A dermoscopic photograph of a skin lesion.
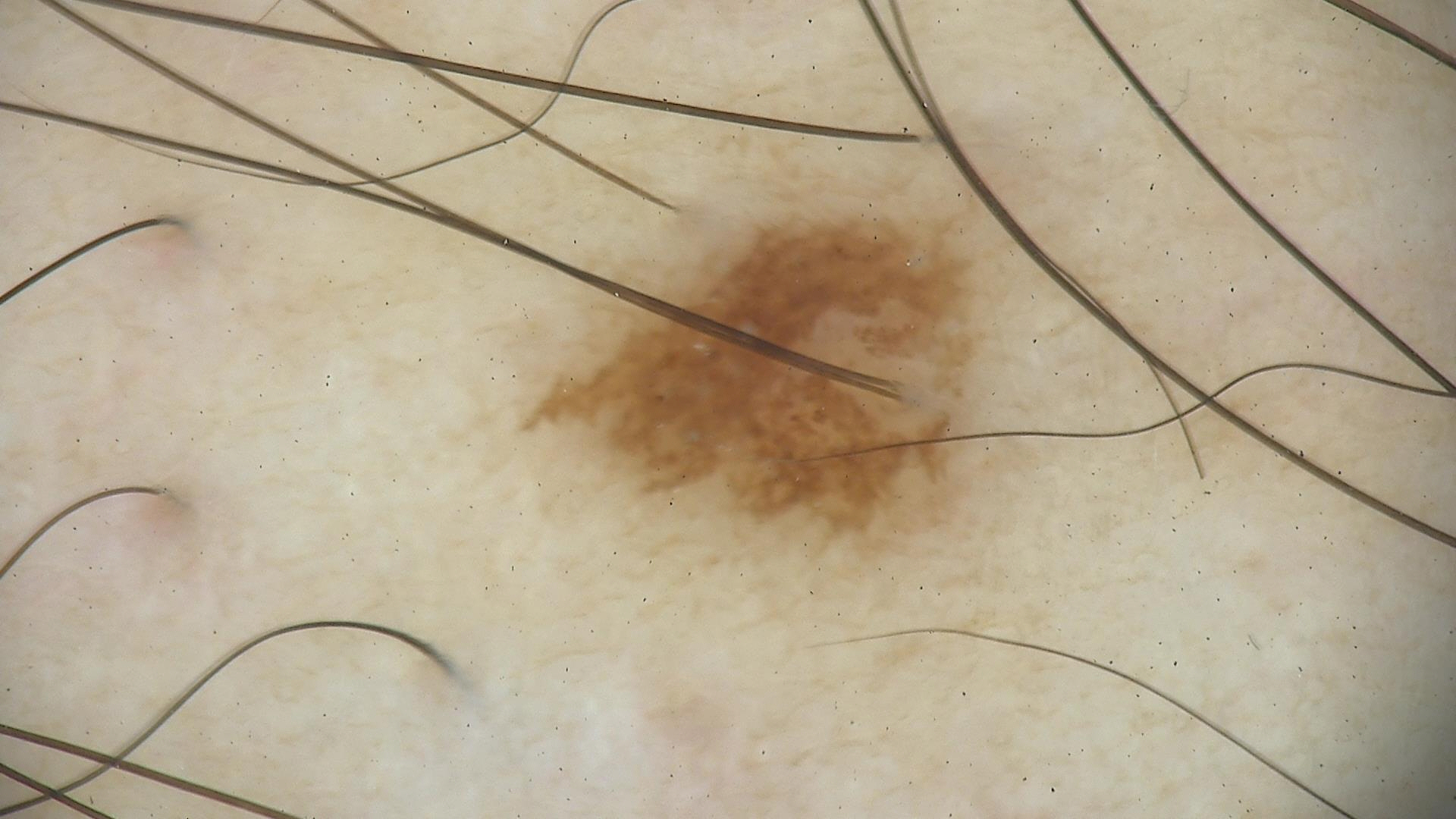Impression:
Consistent with a benign lesion — a dysplastic junctional nevus.